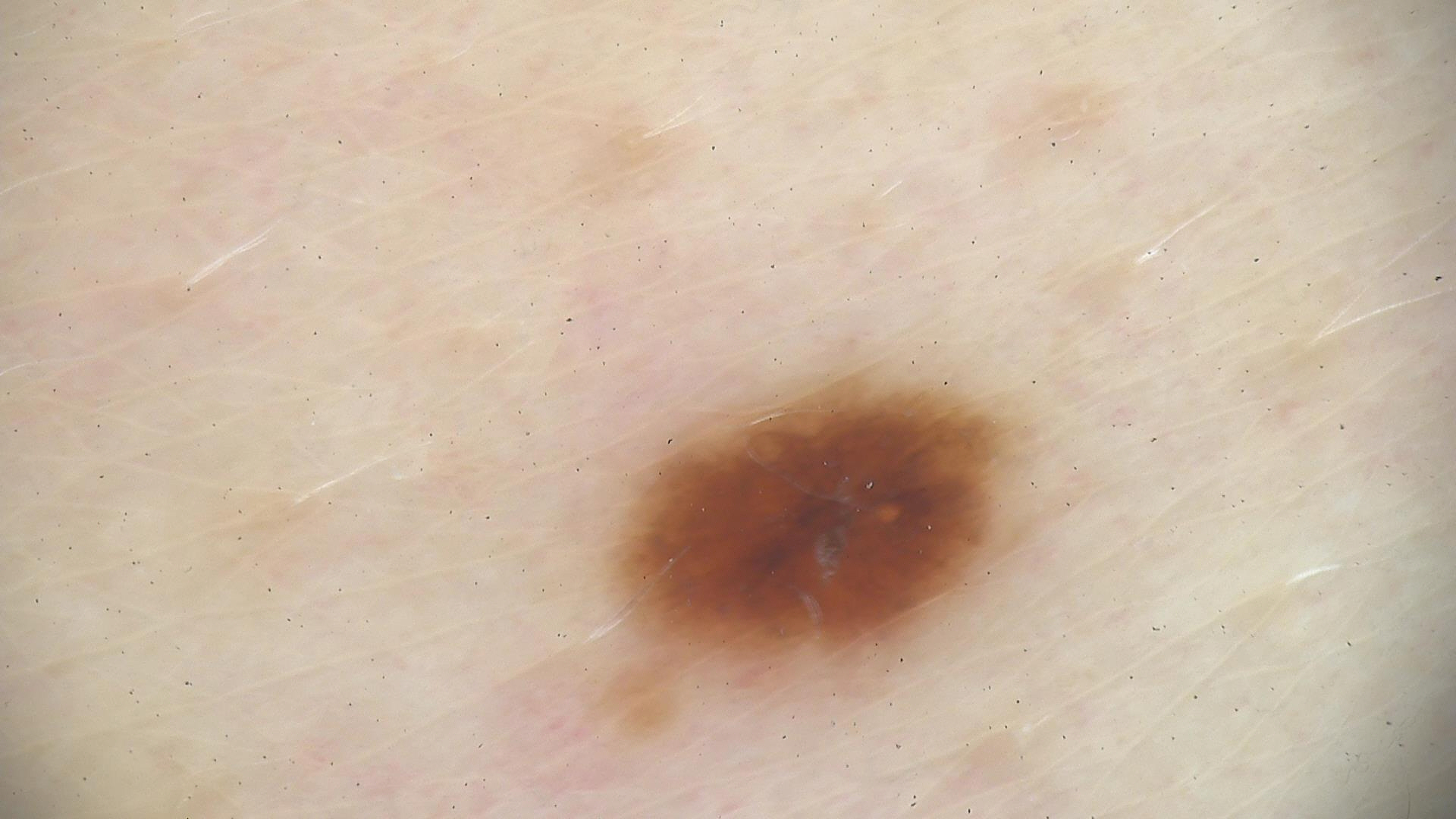  image: dermatoscopy
  diagnosis:
    name: dysplastic junctional nevus
    code: jd
    malignancy: benign
    super_class: melanocytic
    confirmation: expert consensus